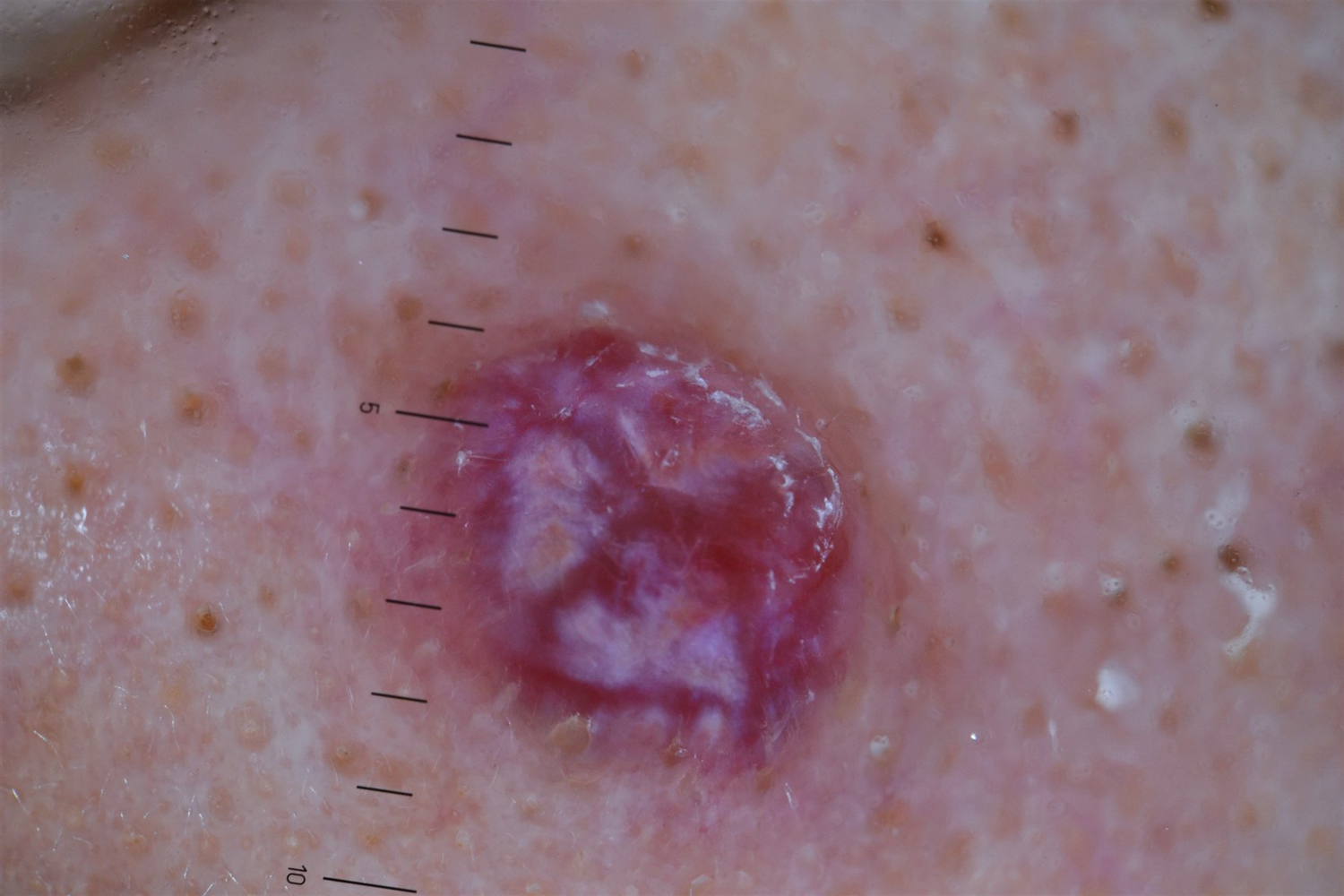modality = dermoscopy, diagnosis = Kaposi sarcoma (biopsy-proven).